Present for one to four weeks. The lesion involves the arm. The photo was captured at an angle. The patient reports the lesion is rough or flaky — 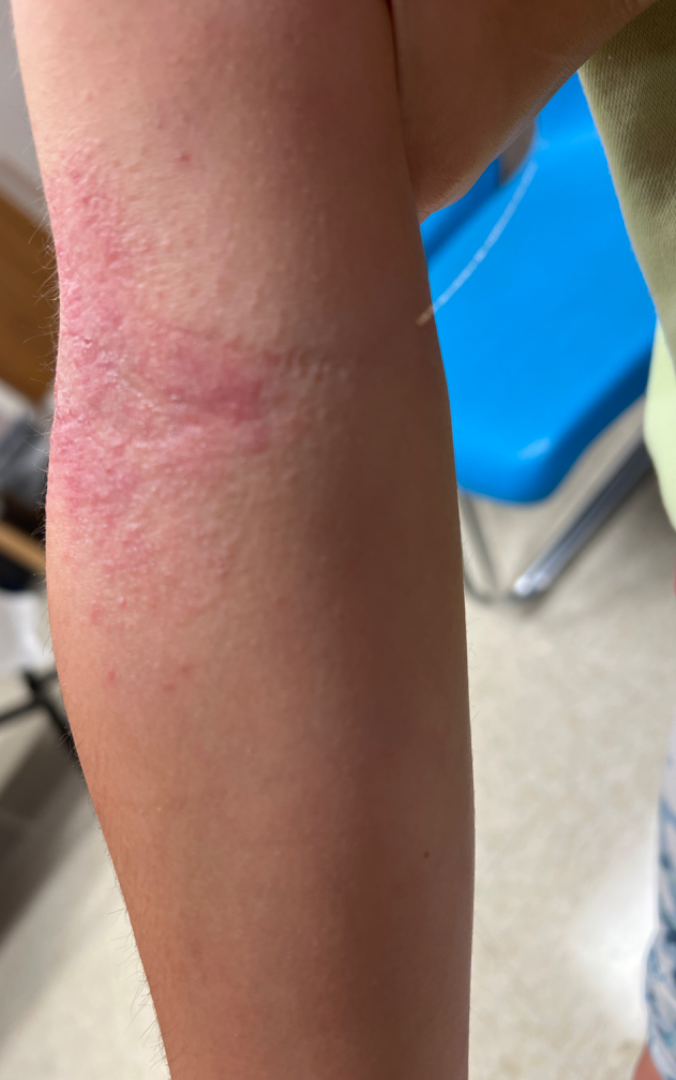Most consistent with Eczema.